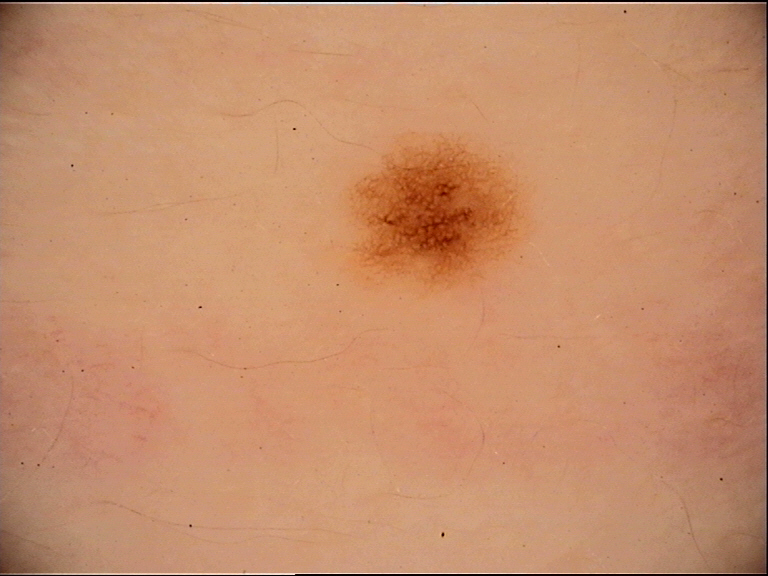Impression: Labeled as a dysplastic junctional nevus.